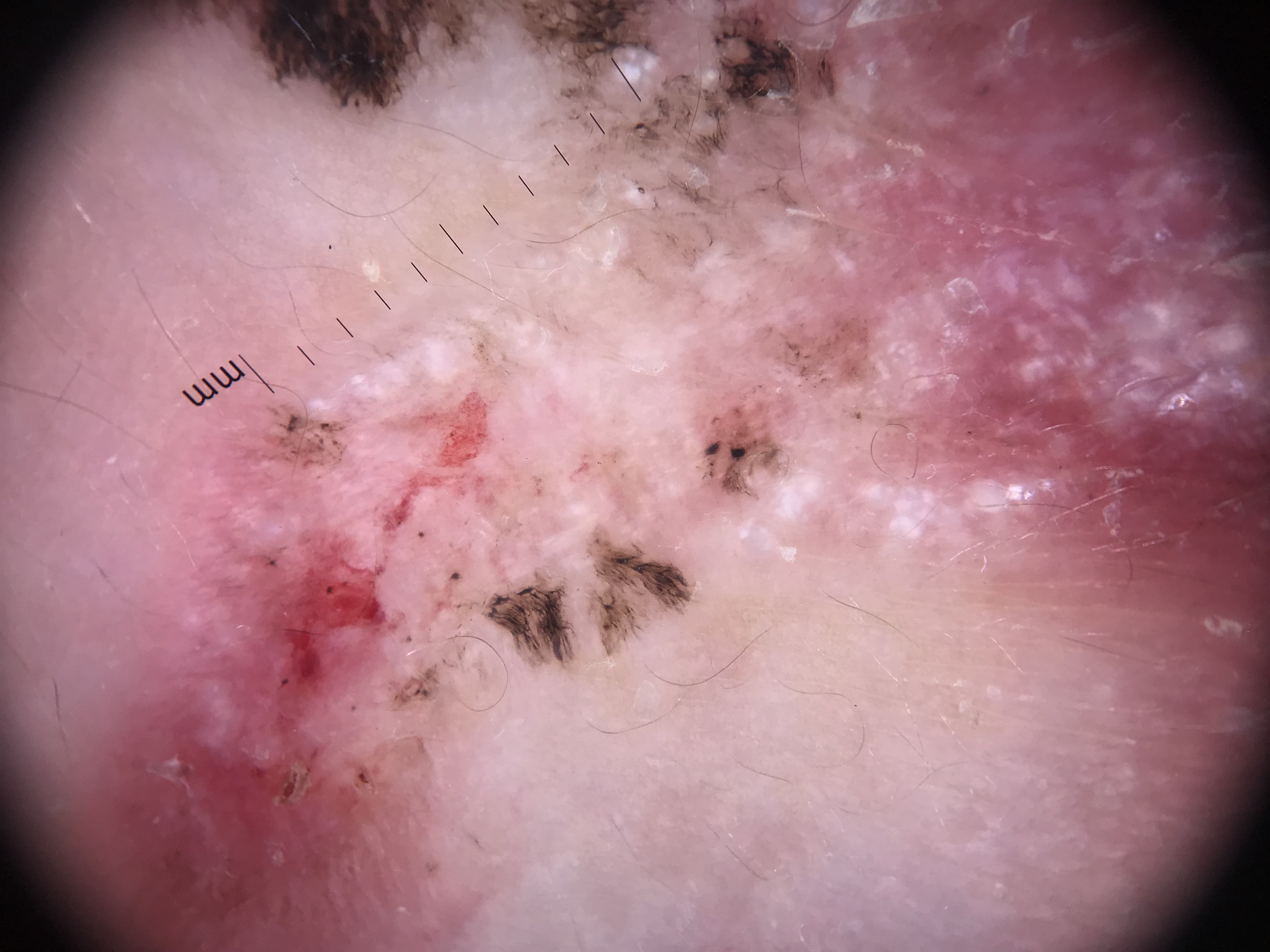Histopathology confirmed a melanoma.